A clinical photo of a skin lesion taken with a smartphone; history notes alcohol use, prior skin cancer (patient or family), and no pesticide exposure; a male patient age 69; the patient was assessed as Fitzpatrick phototype II — 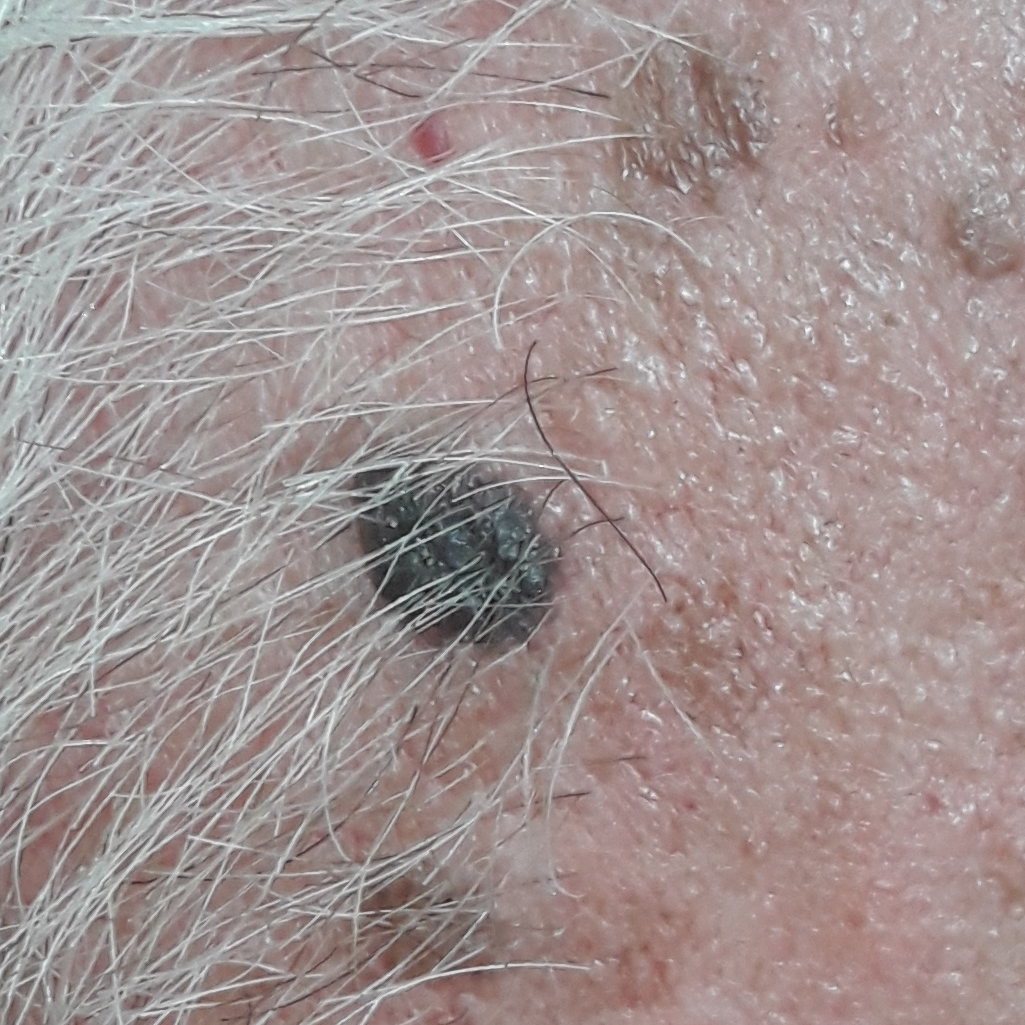Clinical context:
Located on the face. The lesion measures approximately 10 × 5 mm. The patient describes that the lesion is elevated.
Conclusion:
Histopathologically confirmed as a seborrheic keratosis.